The photograph was taken at an angle.
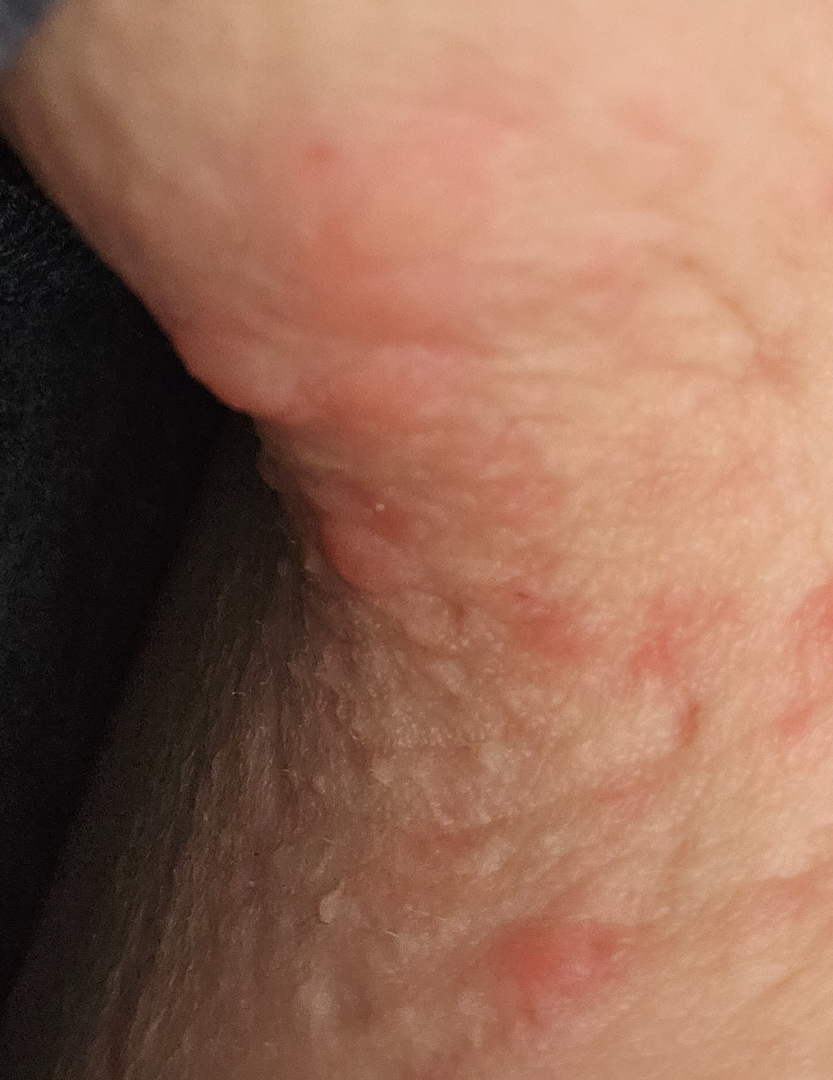| key | value |
|---|---|
| differential | Folliculitis (possible); Herpes Zoster (possible); Allergic Contact Dermatitis (possible) |